A dermoscopic close-up of a skin lesion:
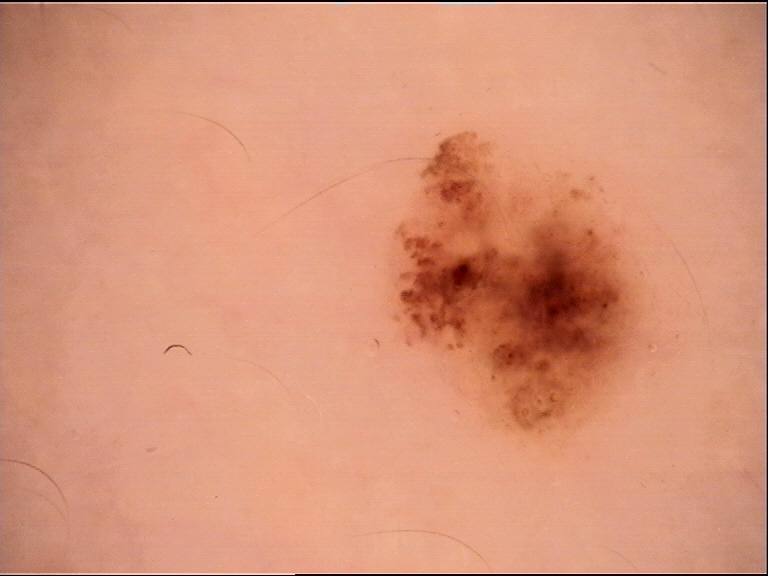Impression:
Diagnosed as a benign lesion — a dysplastic junctional nevus.